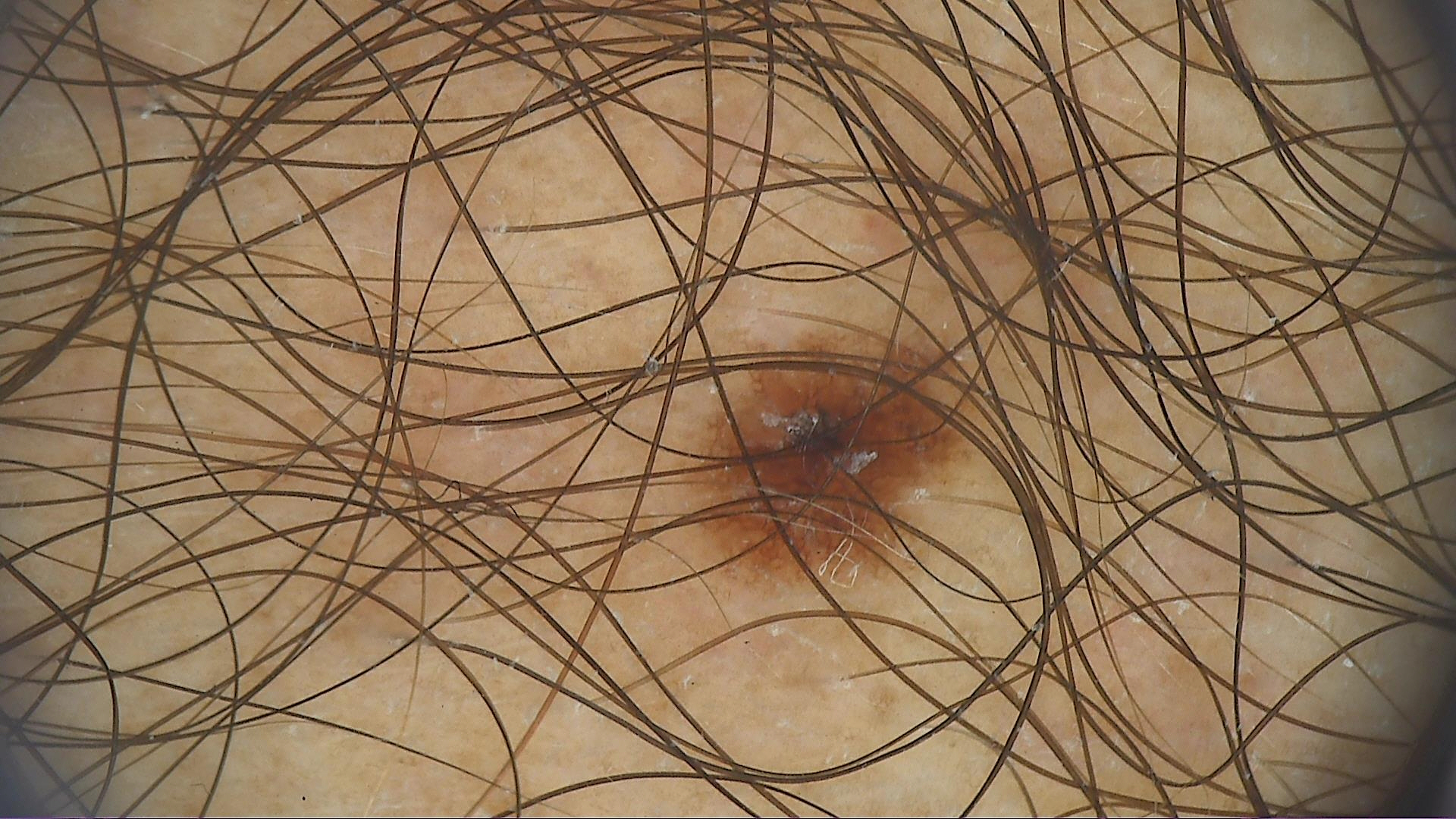Diagnosed as a dysplastic junctional nevus.